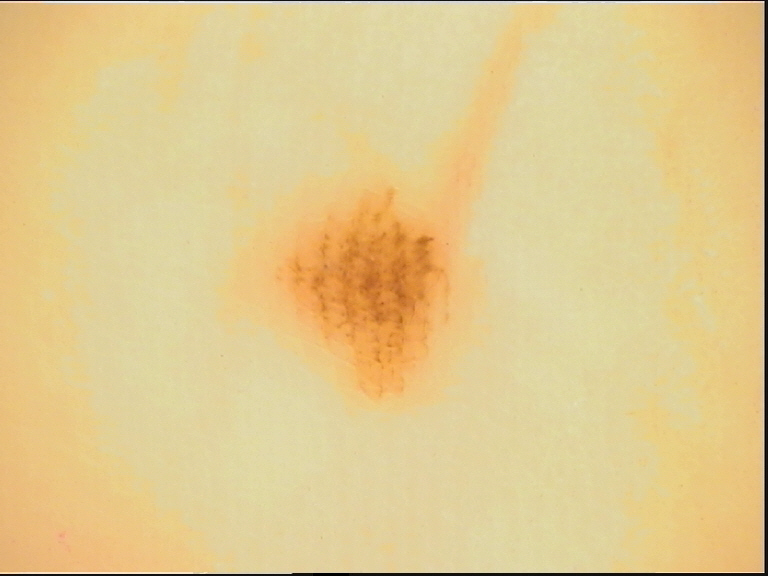Diagnosed as a banal lesion — an acral junctional nevus.